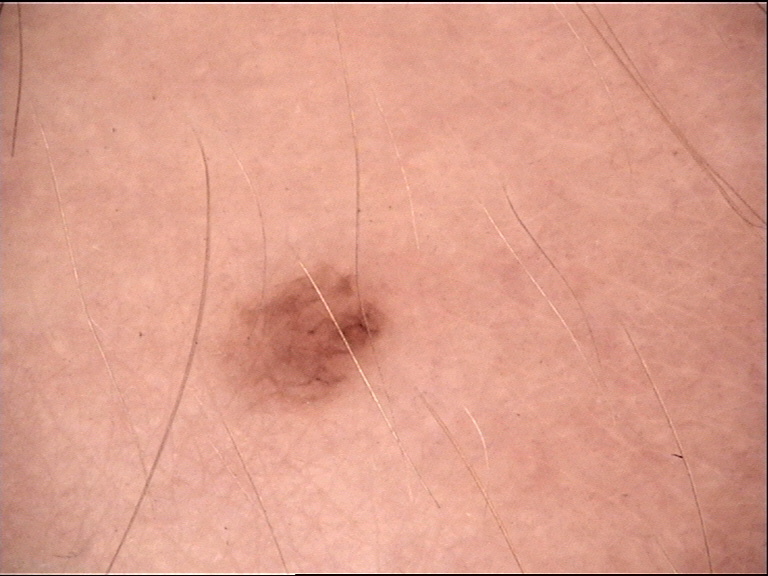A skin lesion imaged with a dermatoscope.
This is a banal lesion.
Labeled as a dermal nevus.